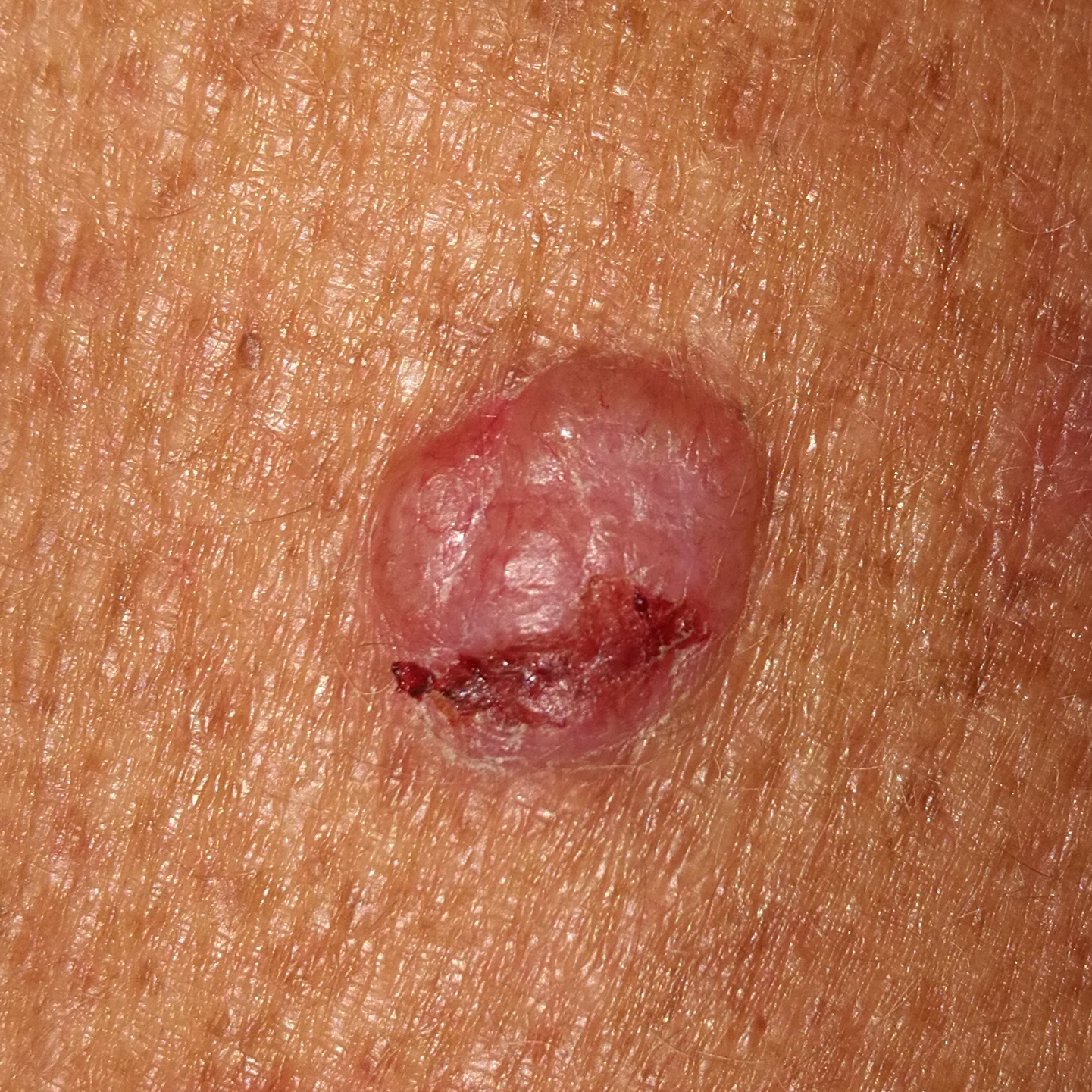Recorded as skin type III. The lesion is located on a forearm. Measuring about 15 × 13 mm. By the patient's account, the lesion has grown, itches, is elevated, and has bled. On biopsy, the diagnosis was a basal cell carcinoma.